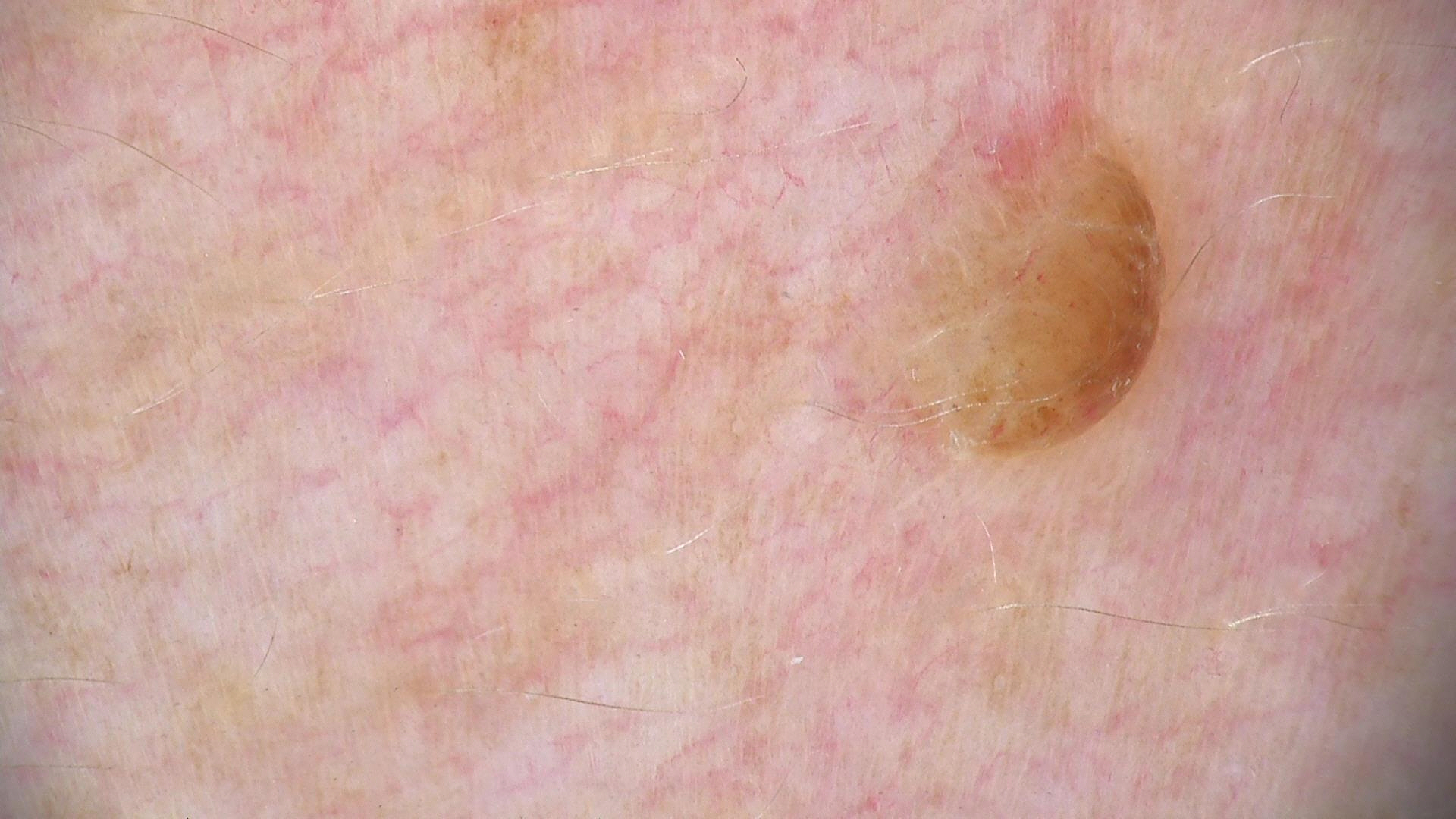A dermatoscopic image of a skin lesion. The morphology is that of a banal lesion. The diagnostic label was a dermal nevus.